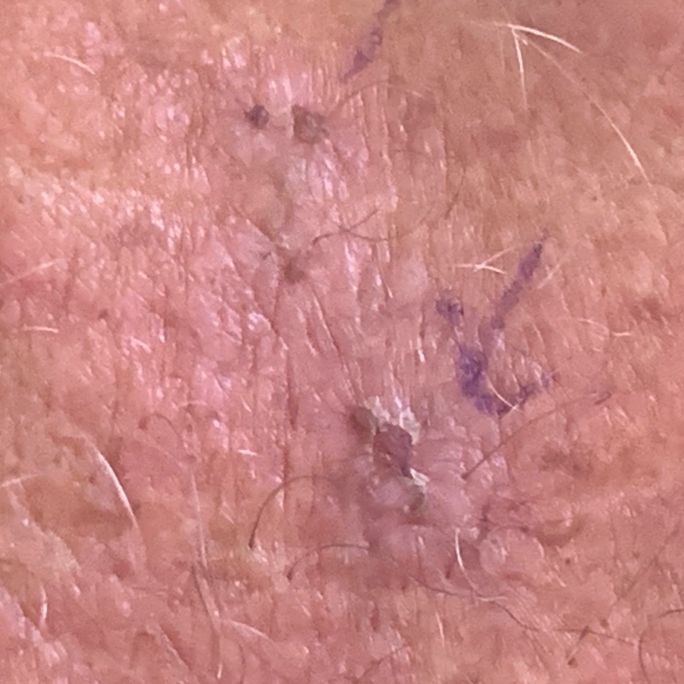image type — clinical photograph; patient — in their 50s; body site — the chest; patient-reported symptoms — itching; assessment — actinic keratosis (clinical consensus).